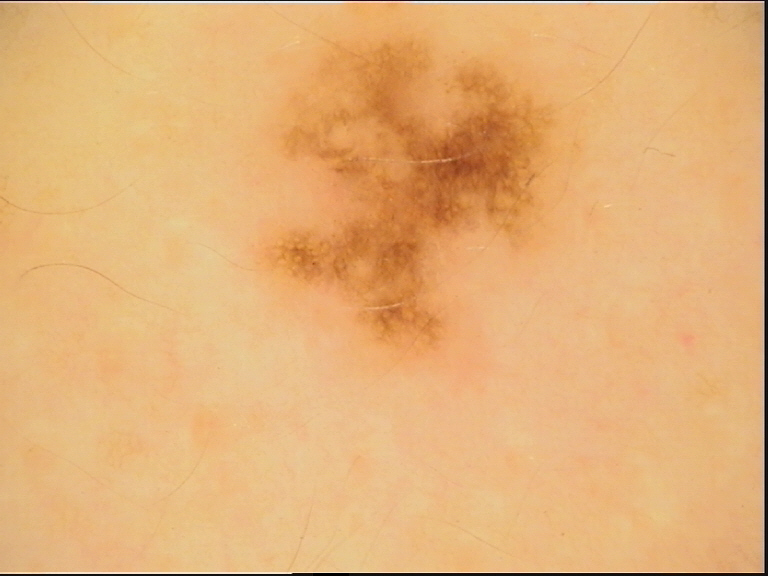A dermoscopic photograph of a skin lesion. Classified as a benign lesion — a dysplastic junctional nevus.